The patient says their skin reddens with sun exposure. On a questionnaire the patient reported a personal history of skin cancer and a personal history of cancer. A dermoscopic image of a skin lesion. The patient describes having few moles overall. Imaged for a research study, with no referral diagnosis recorded.
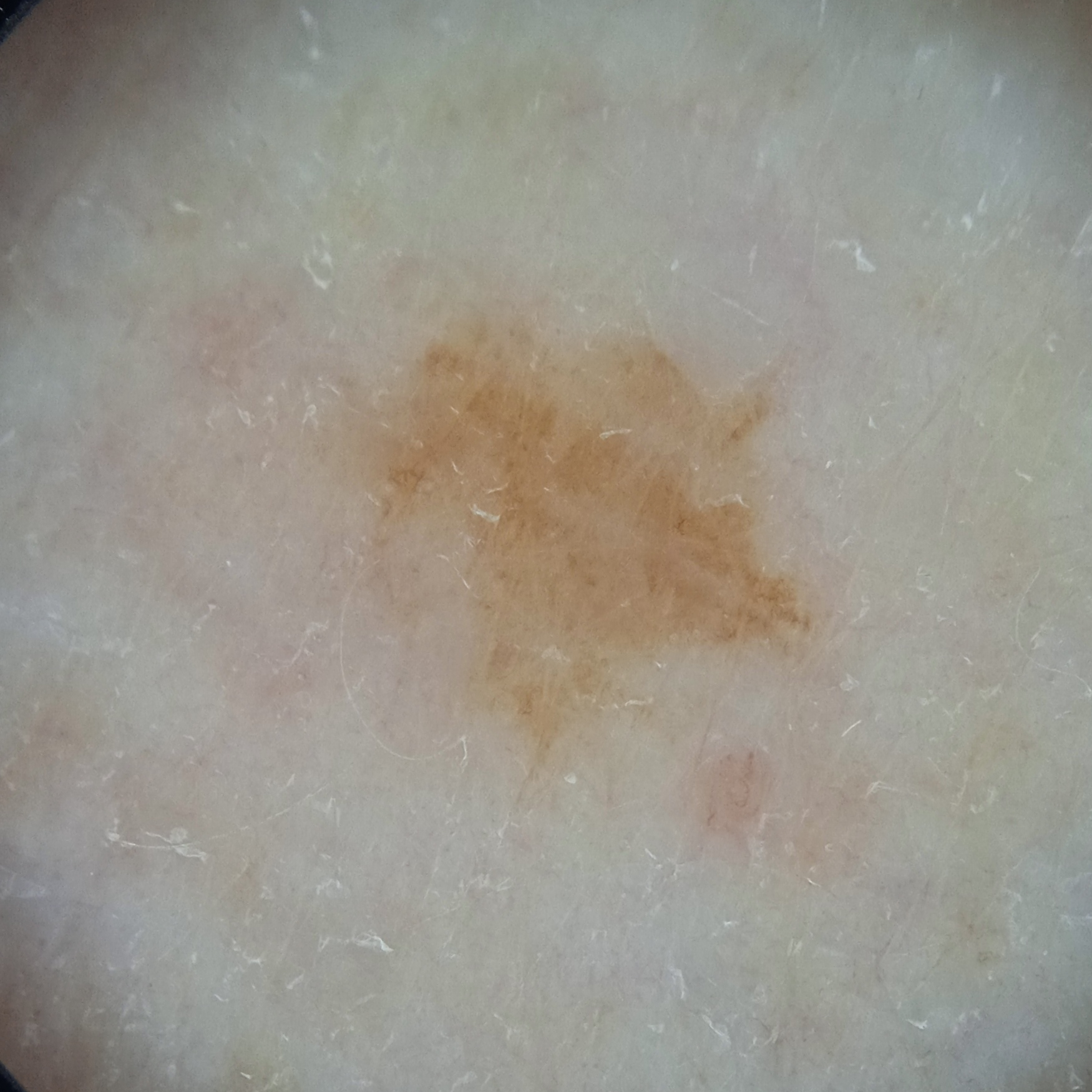{
  "lesion_location": "an arm",
  "diagnosis": {
    "name": "melanocytic nevus",
    "malignancy": "benign"
  }
}